A close-up photograph, the affected area is the back of the hand.
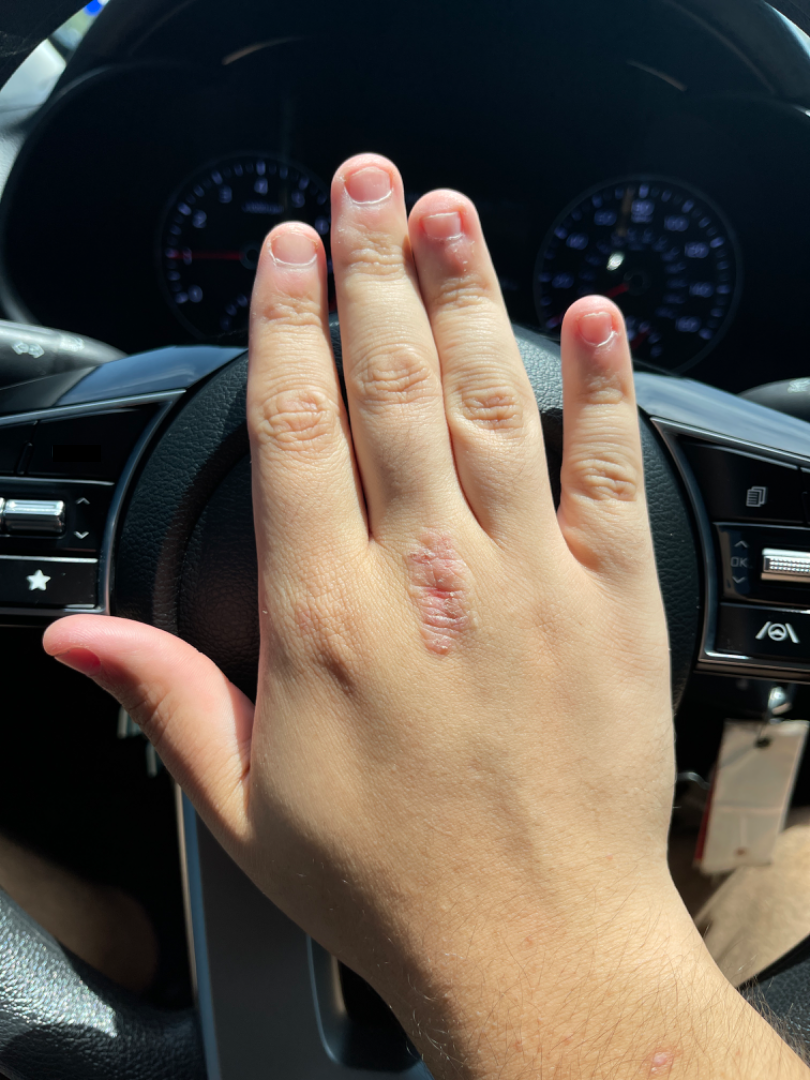patient describes the issue as: a rash; surface texture: rough or flaky and raised or bumpy; onset: one to three months; reported symptoms: bothersome appearance, enlargement and itching; dermatologist impression: consistent with Verruca vulgaris.